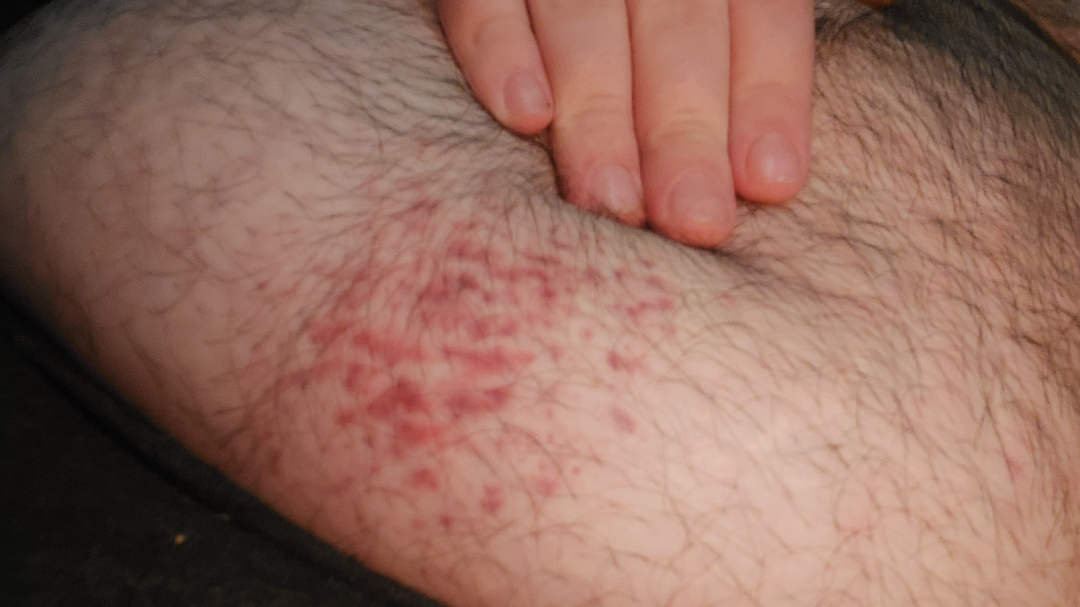The reviewer was unable to grade this case for skin condition. Male contributor, age 18–29. The lesion is described as flat. This image was taken at a distance. The front of the torso is involved. Skin tone: Fitzpatrick skin type II.